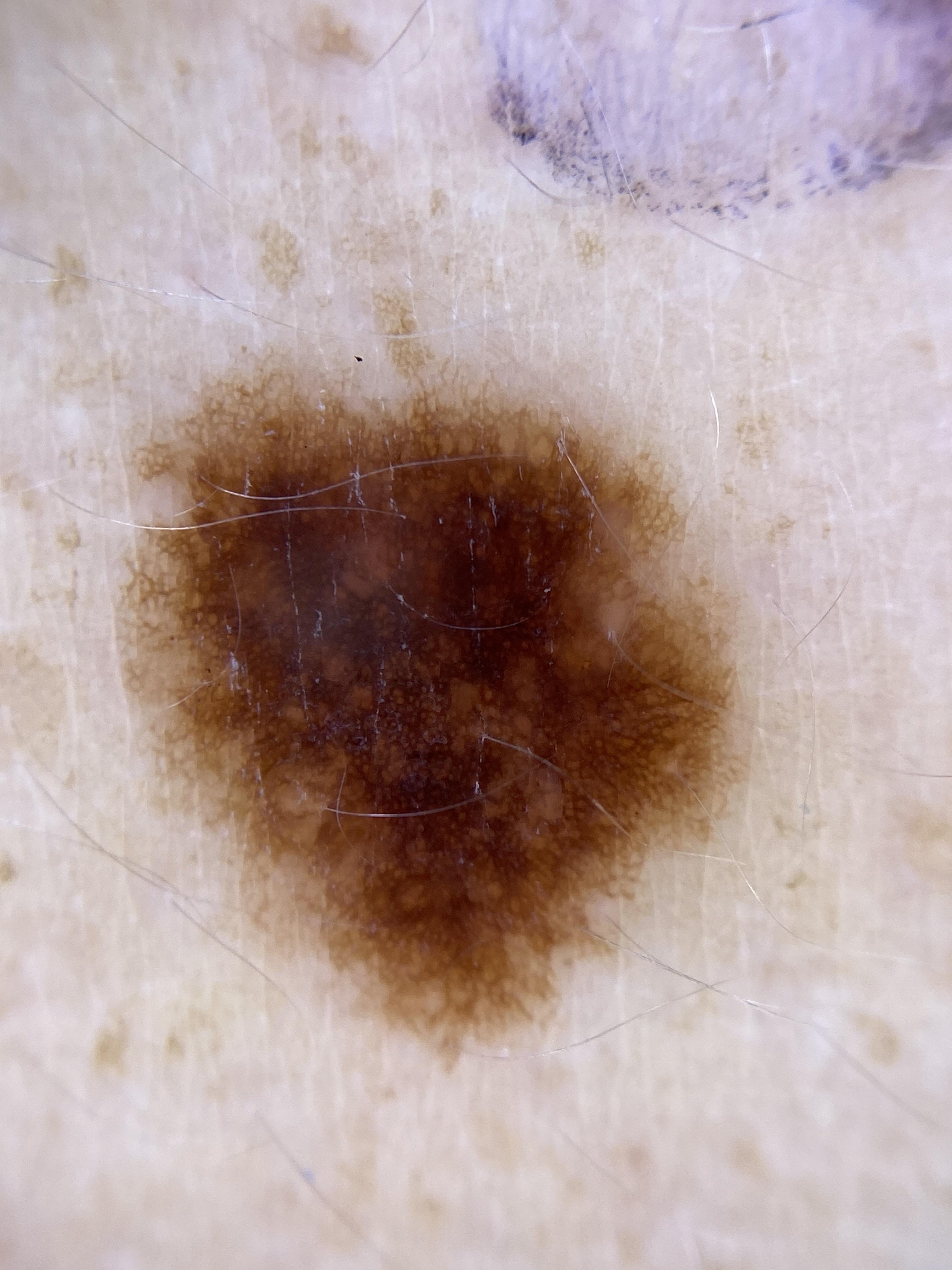– Fitzpatrick: II
– patient: male, aged approximately 35
– image: dermoscopic image
– risk factors: a first-degree relative with melanoma
– site: an upper extremity
– diagnosis: Nevus (biopsy-proven)